Collected as part of a research study, without a referral diagnosis. The patient says their skin reddens with sun exposure. A male patient 72 years of age:
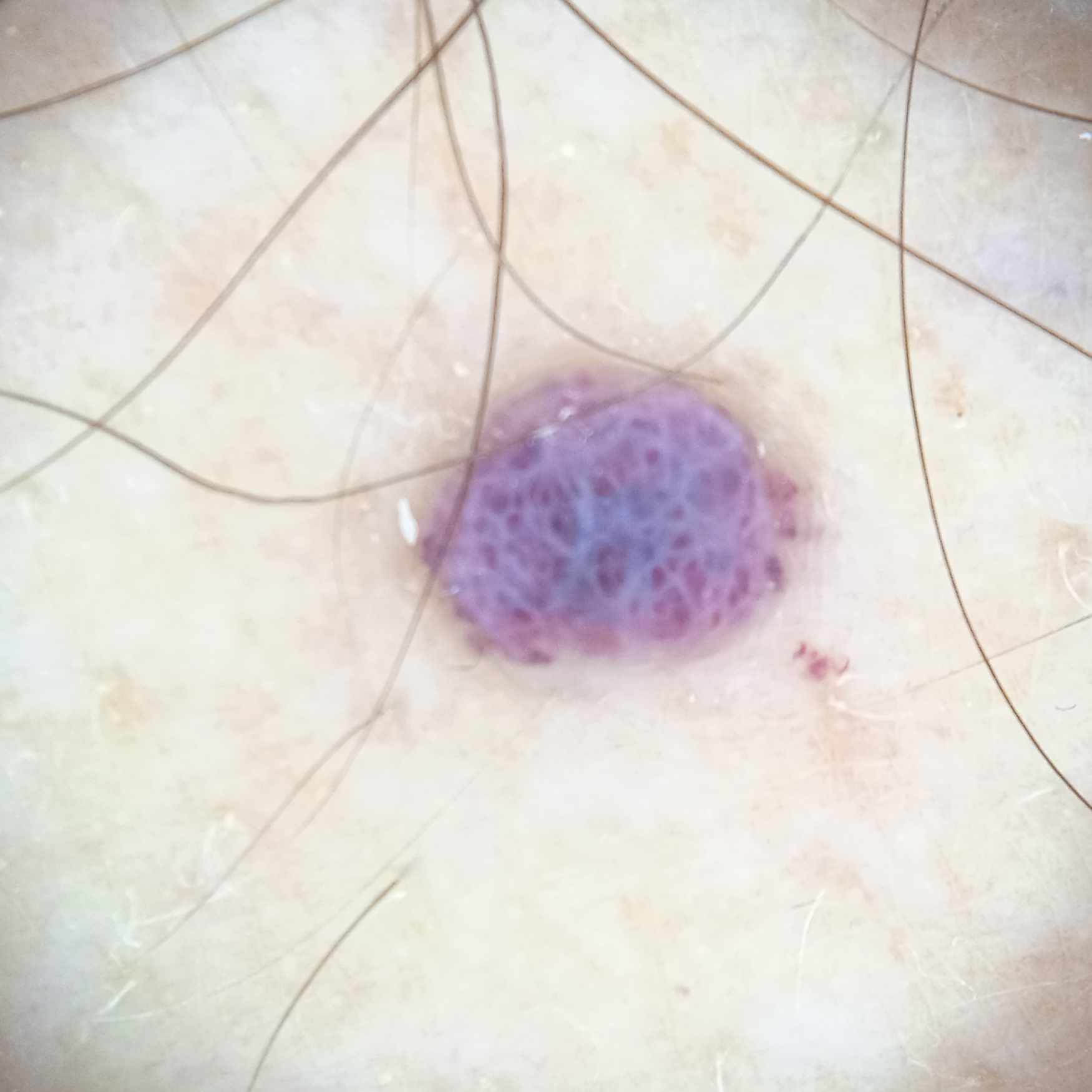body site — the torso; lesion size — 4.7 mm; diagnostic label — angioma (dermatologist consensus).